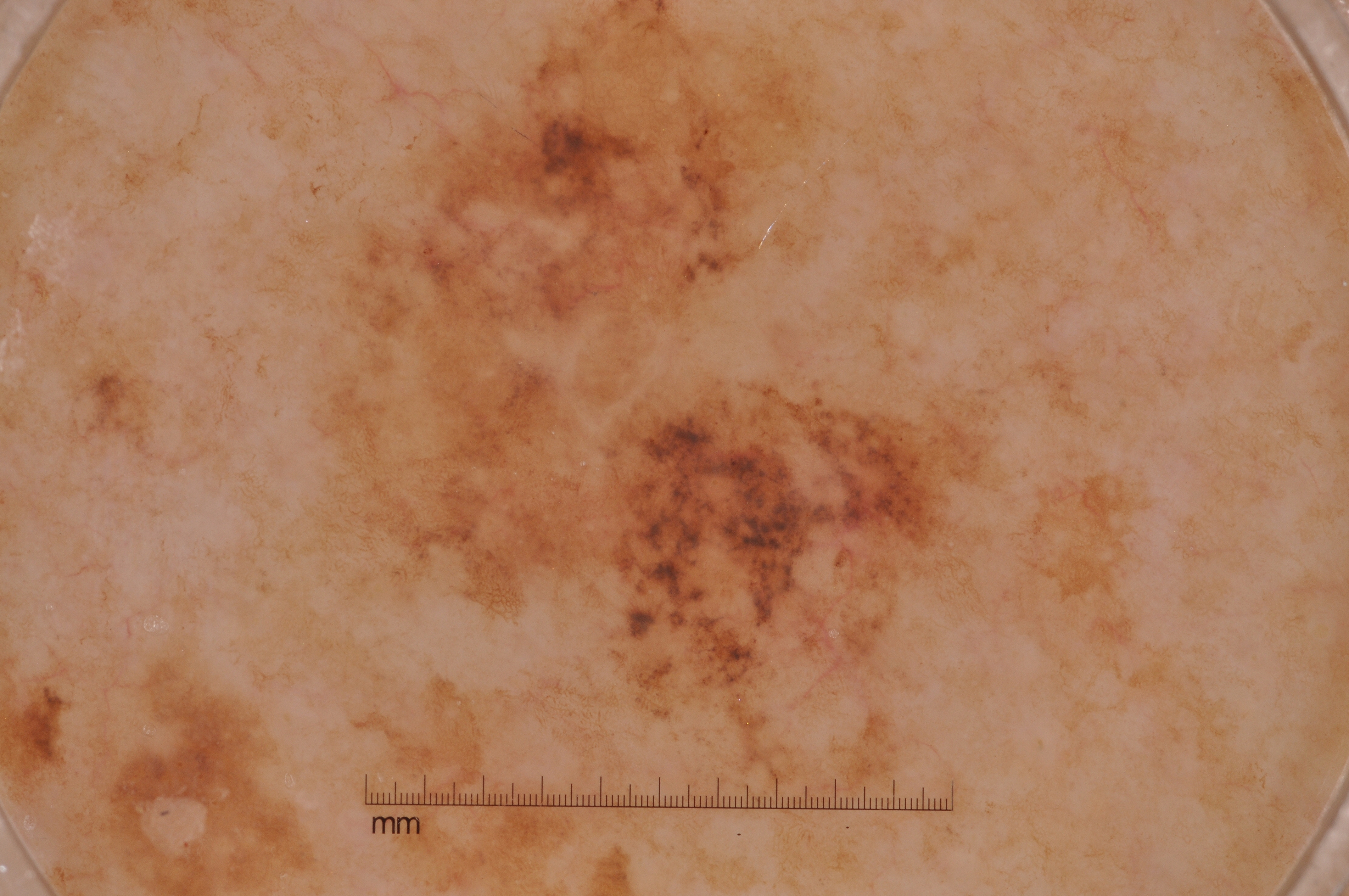Image and clinical context:
This is a dermoscopic photograph of a skin lesion. Lesion location: x1=298, y1=5, x2=1002, y2=797.
Pathology:
On biopsy, the diagnosis was a melanoma.